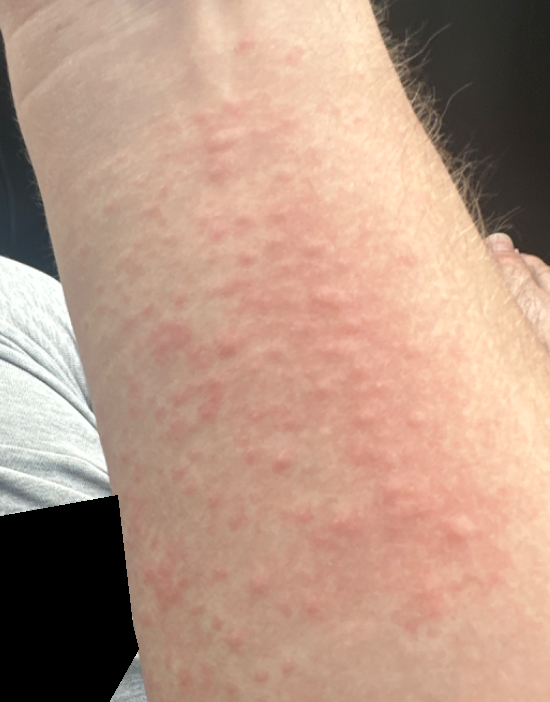| field | value |
|---|---|
| systemic symptoms | none reported |
| image framing | close-up |
| contributor | male |
| lesion texture | raised or bumpy |
| patient's own categorization | a rash |
| skin tone | Fitzpatrick II |
| anatomic site | arm |
| symptom duration | about one day |
| diagnostic considerations | favoring Urticaria |